Located on the arm. An image taken at a distance:
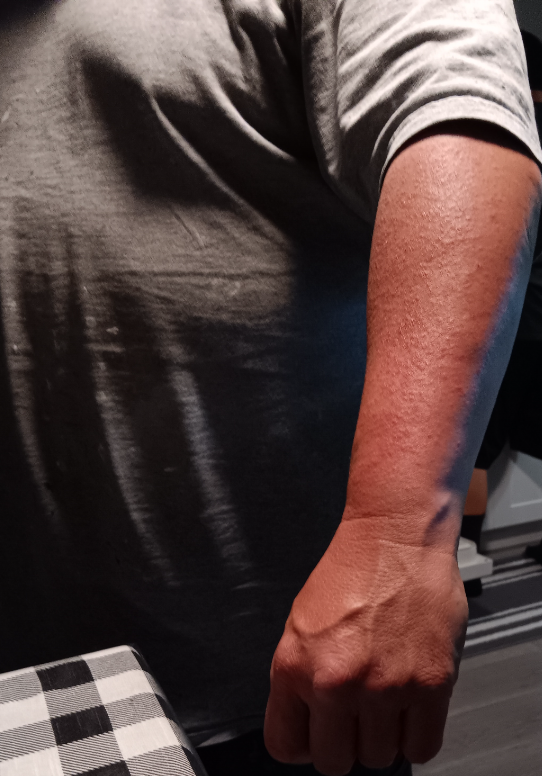Q: What was the assessment?
A: indeterminate